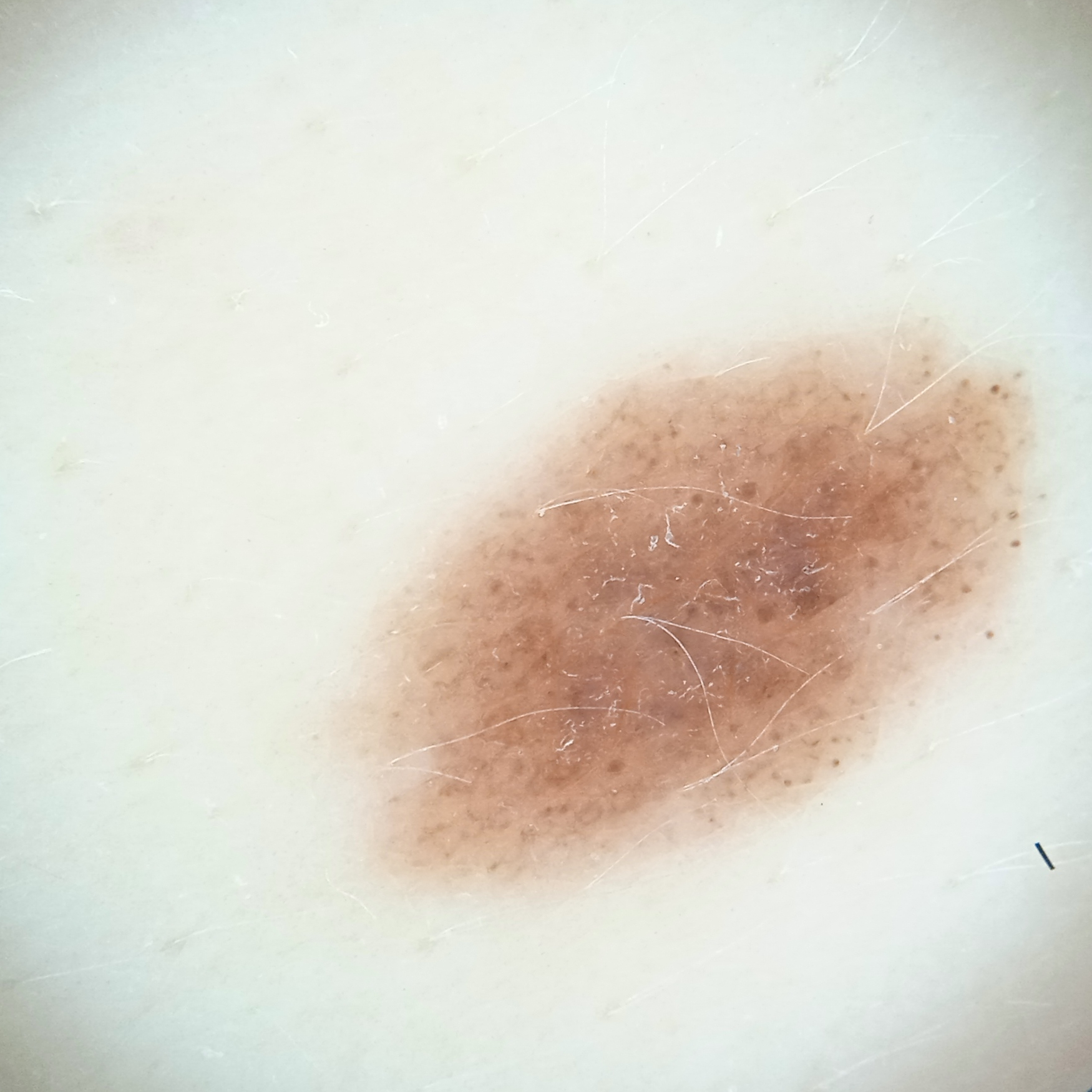Case:
* imaging · dermatoscopic image
* subject · female, 27 years of age
* nevus count · a moderate number of melanocytic nevi
* sun reaction · skin reddens with sun exposure
* referral context · research study (no referral diagnosis)
* body site · the back
* diameter · 9.4 mm
* diagnostic label · melanocytic nevus (dermatologist consensus)